The patient describes having few moles overall. The patient says their skin tans without first burning. Dermoscopy of a skin lesion. Imaged for a research study, with no referral diagnosis recorded: 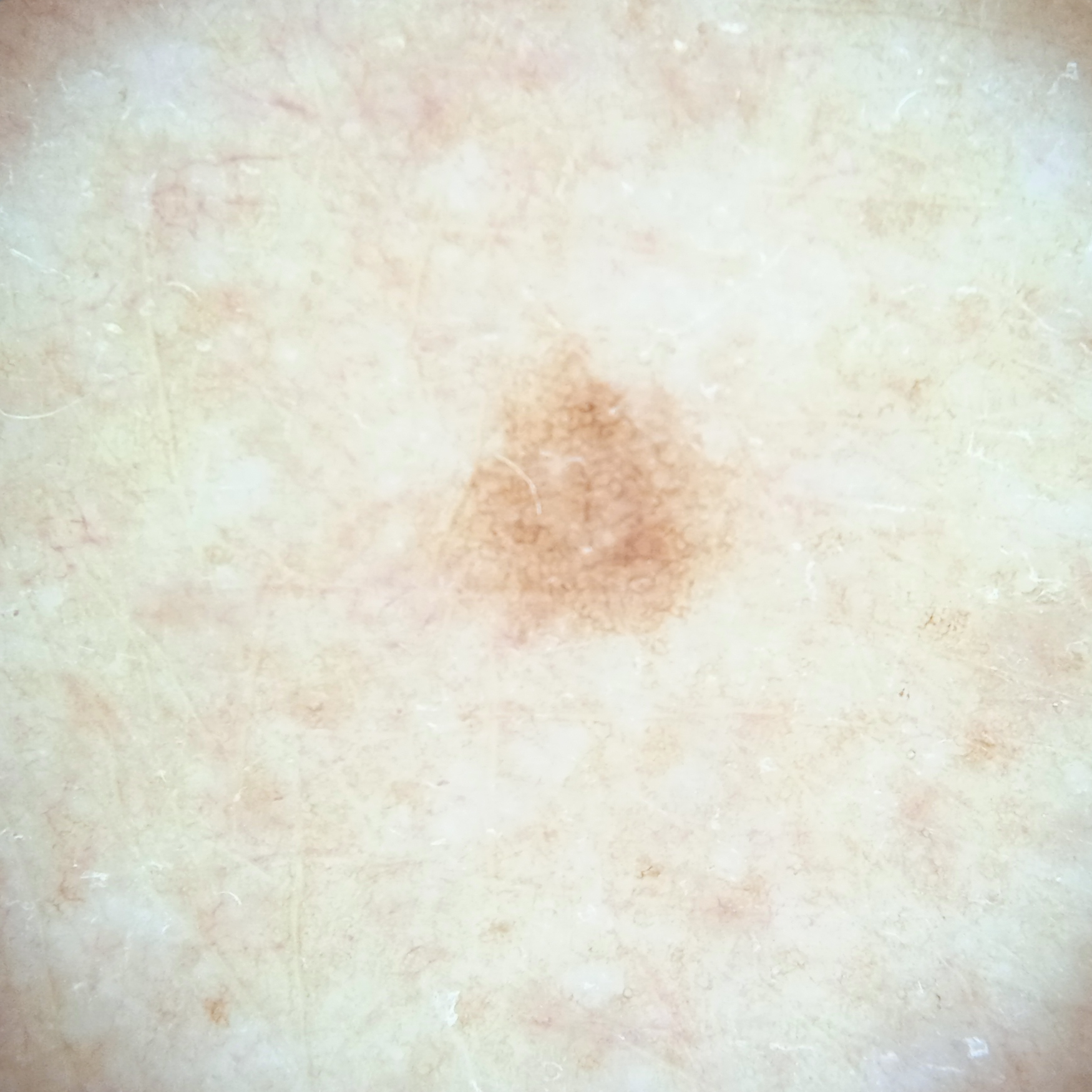Case summary: The lesion involves an arm. The lesion is about 2.8 mm across. Conclusion: The lesion was assessed as a melanocytic nevus.